The top or side of the foot is involved; reported duration is more than five years; close-up view; the subject is male; the patient indicates itching and bothersome appearance: 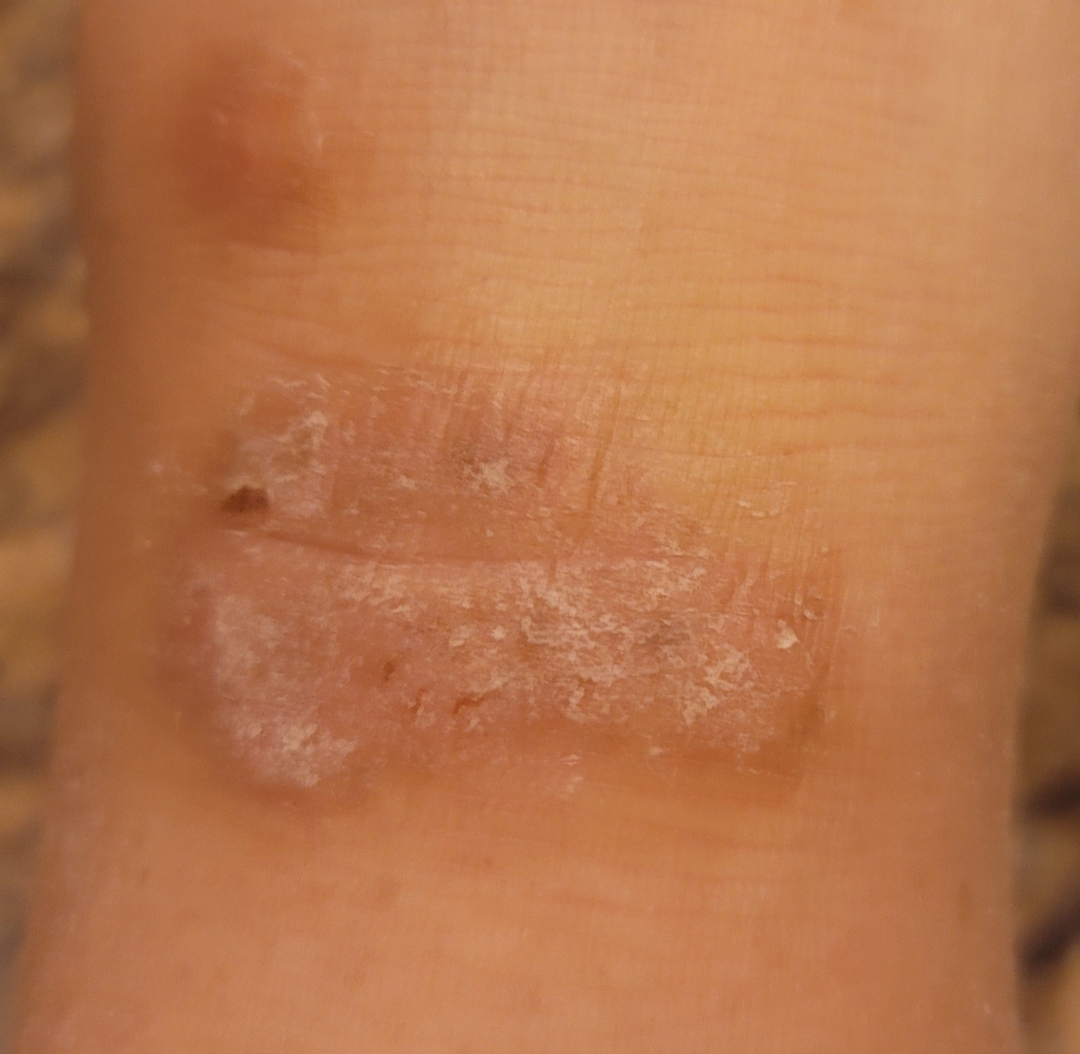On photographic review: the leading impression is Lichen Simplex Chronicus; possibly Eczema; lower on the differential is Psoriasis; less likely is Pemphigus vulgaris.